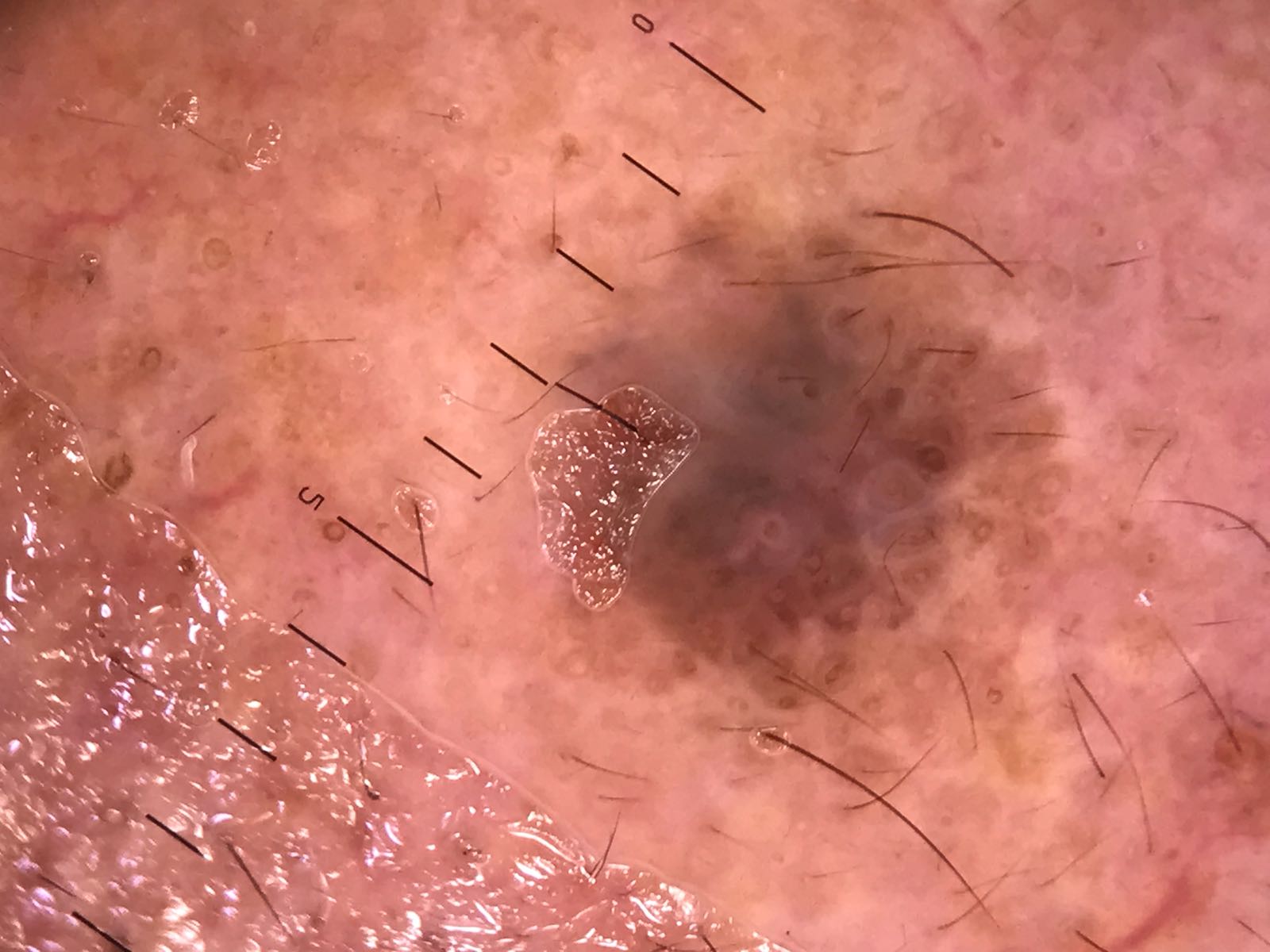The diagnosis was a seborrheic keratosis.